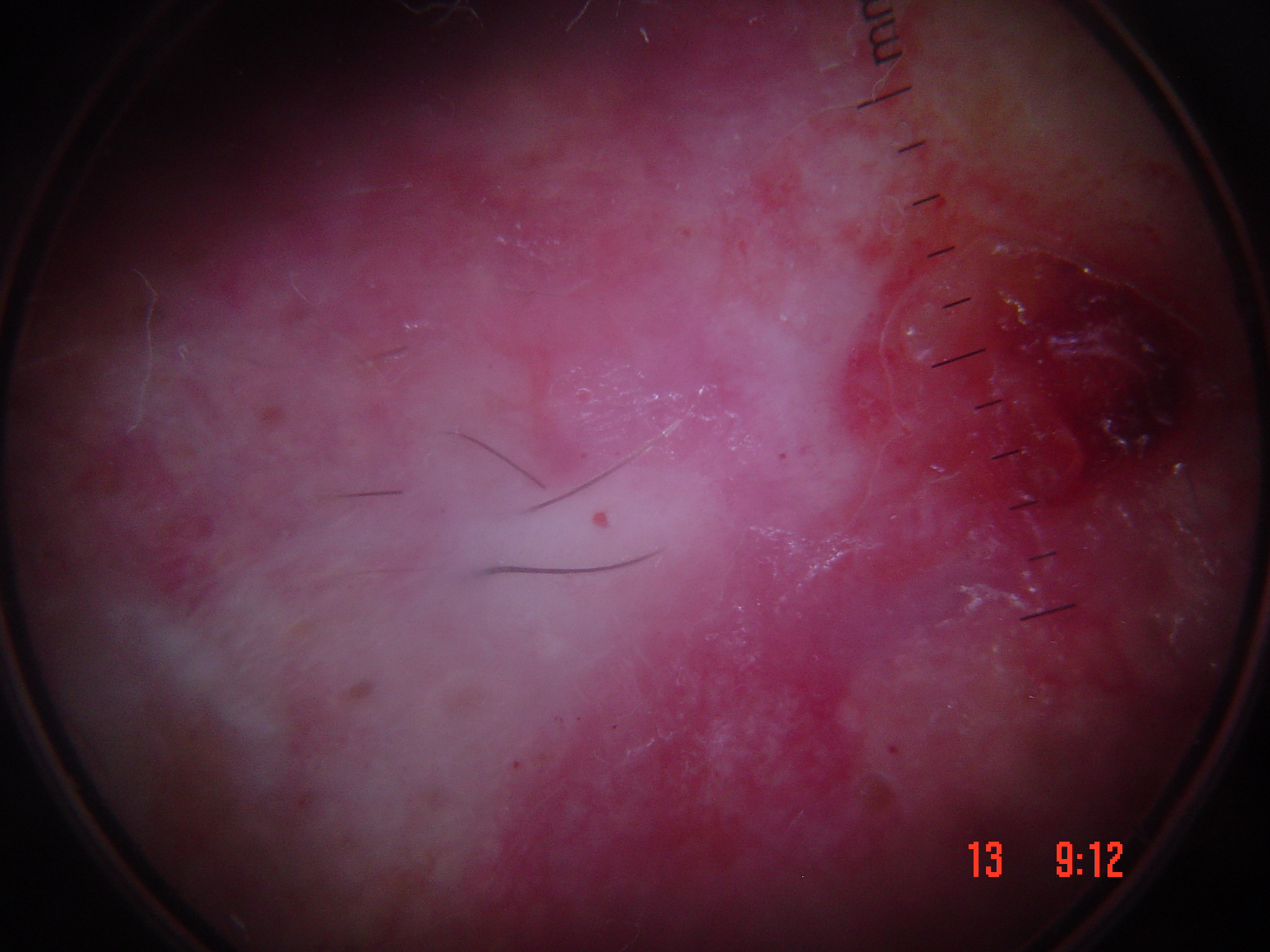Dermoscopy of a skin lesion. Confirmed on histopathology as a keratinocytic lesion — a squamous cell carcinoma.